Located on the leg and top or side of the foot. Texture is reported as fluid-filled. This image was taken at an angle.
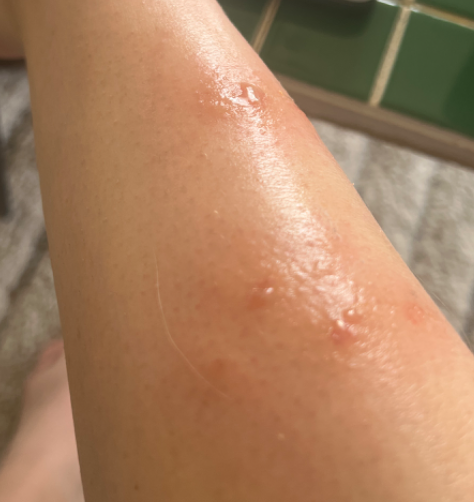On photographic review: Eczema (weight 1.00).